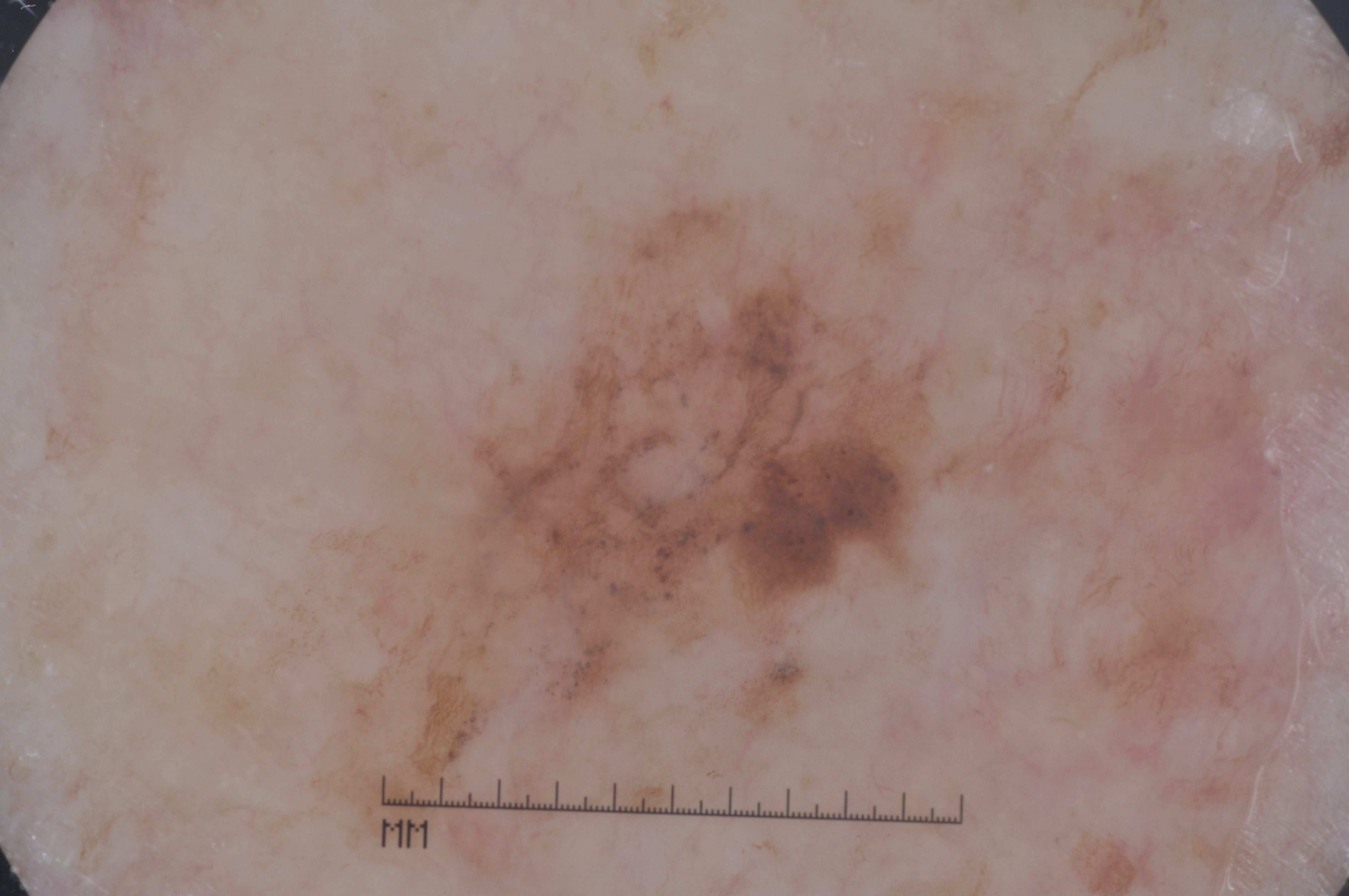Summary:
Dermoscopy of a skin lesion. The patient is a male roughly 80 years of age. The lesion takes up about 29% of the image. On dermoscopy, the lesion shows negative network, pigment network, and milia-like cysts. As (left, top, right, bottom), the lesion is bounded by [219,164,1043,833].
Conclusion:
Histopathology confirmed a melanoma.